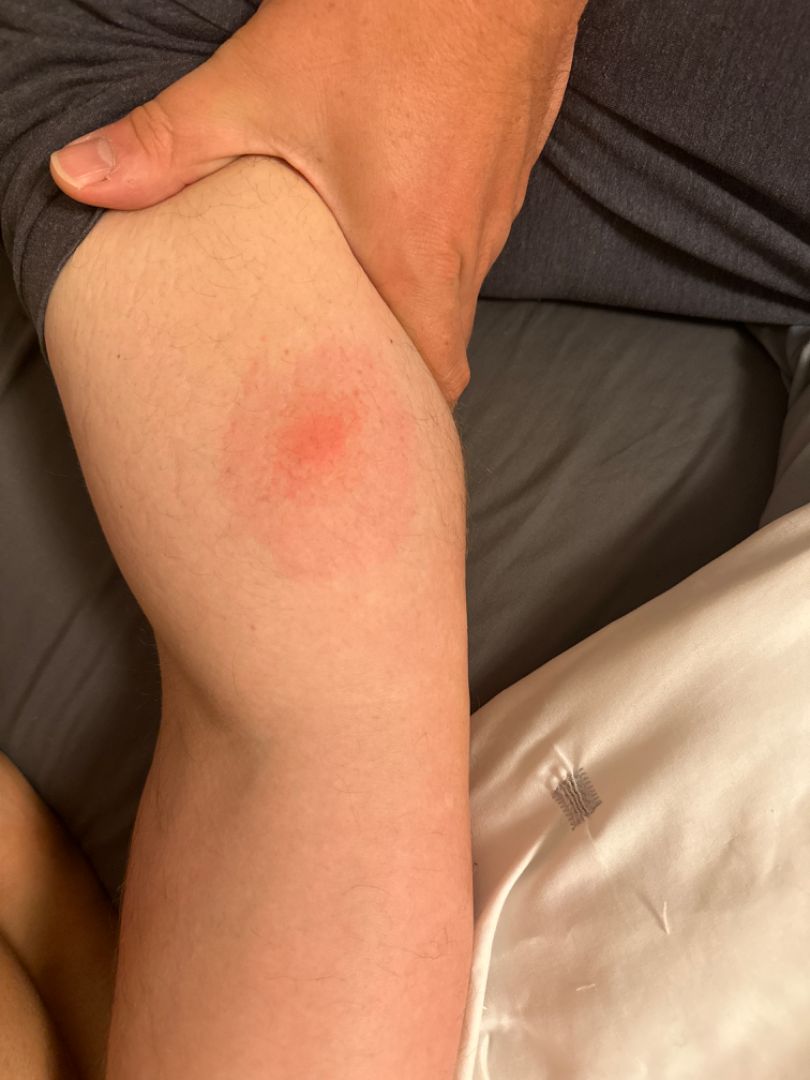Self-categorized by the patient as a rash. The condition has been present for less than one week. The photograph was taken at a distance. The arm is involved. Fitzpatrick IV. The lesion is described as raised or bumpy. On remote review of the image: most consistent with Erythema migrans; an alternative is Cellulitis; with consideration of Insect Bite.